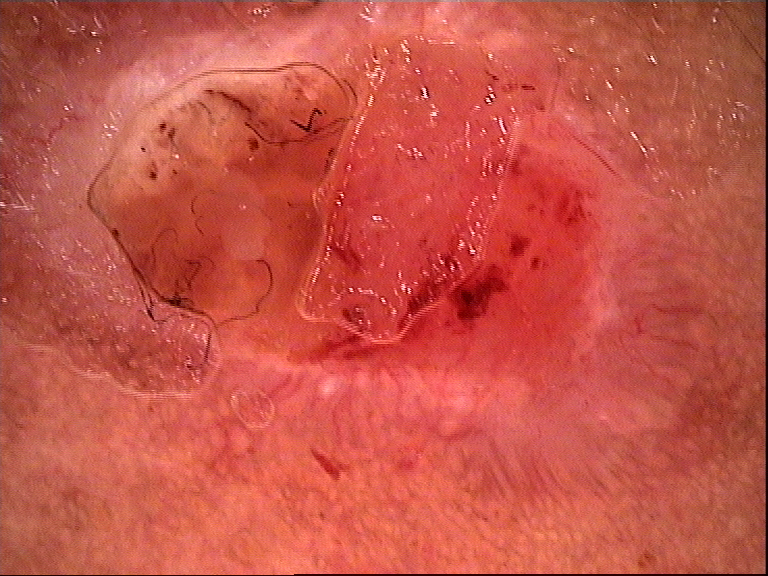{"image": "dermoscopy", "diagnosis": {"name": "squamous cell carcinoma", "code": "scc", "malignancy": "malignant", "super_class": "non-melanocytic", "confirmation": "histopathology"}}